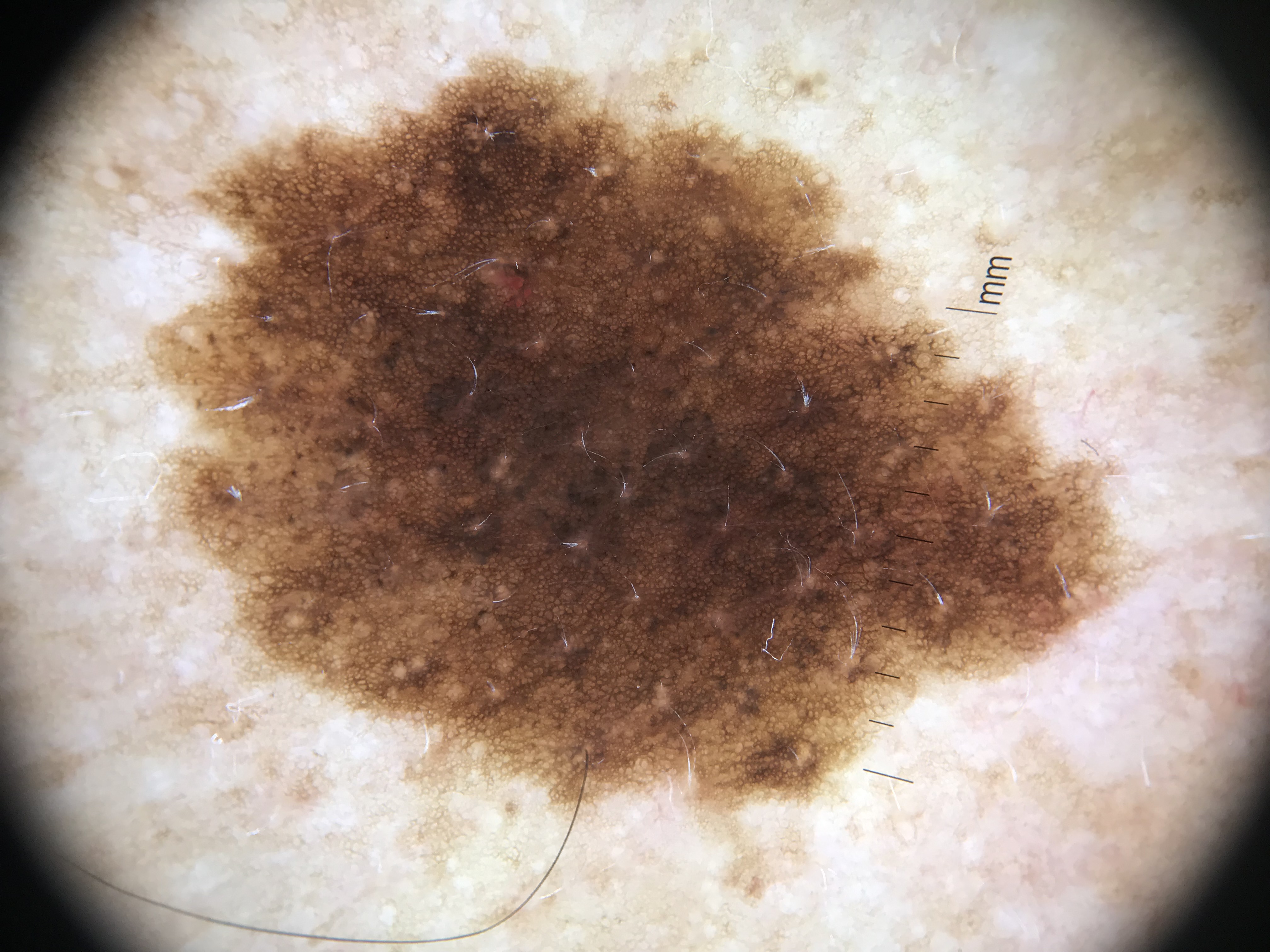- image type: dermatoscopy
- class: dysplastic compound nevus (expert consensus)